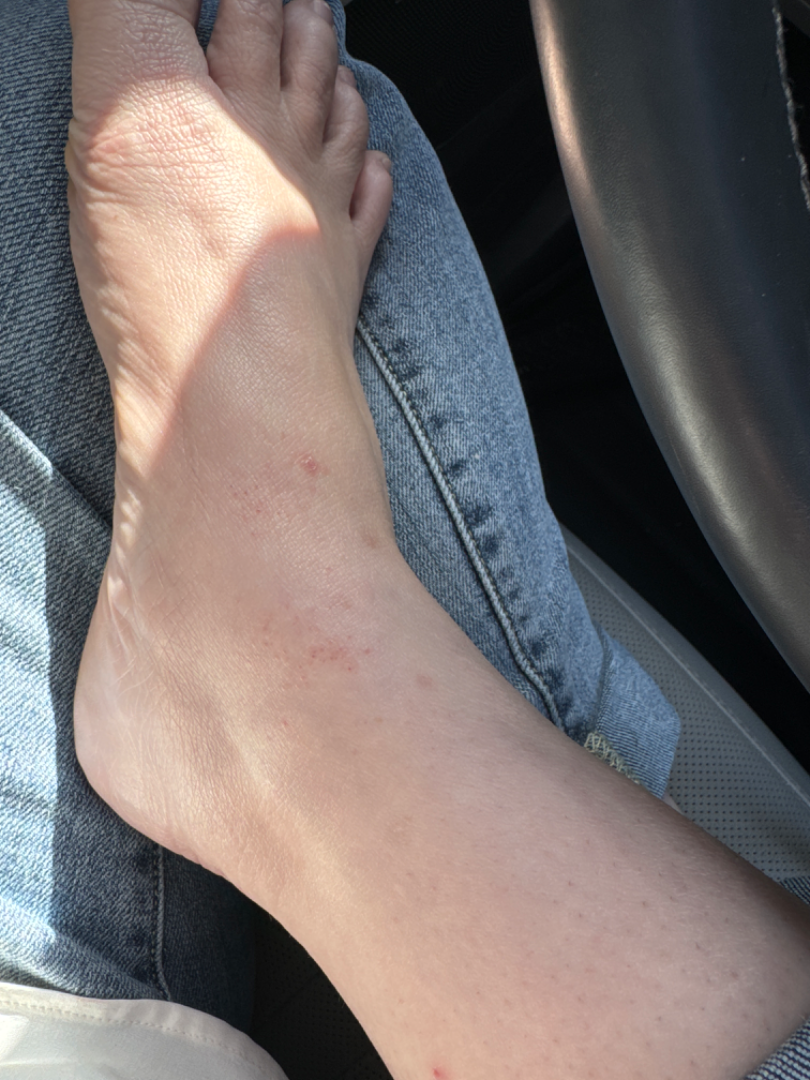Q: What is the differential diagnosis?
A: the differential, in no particular order, includes Pigmented purpuric eruption and Eczema